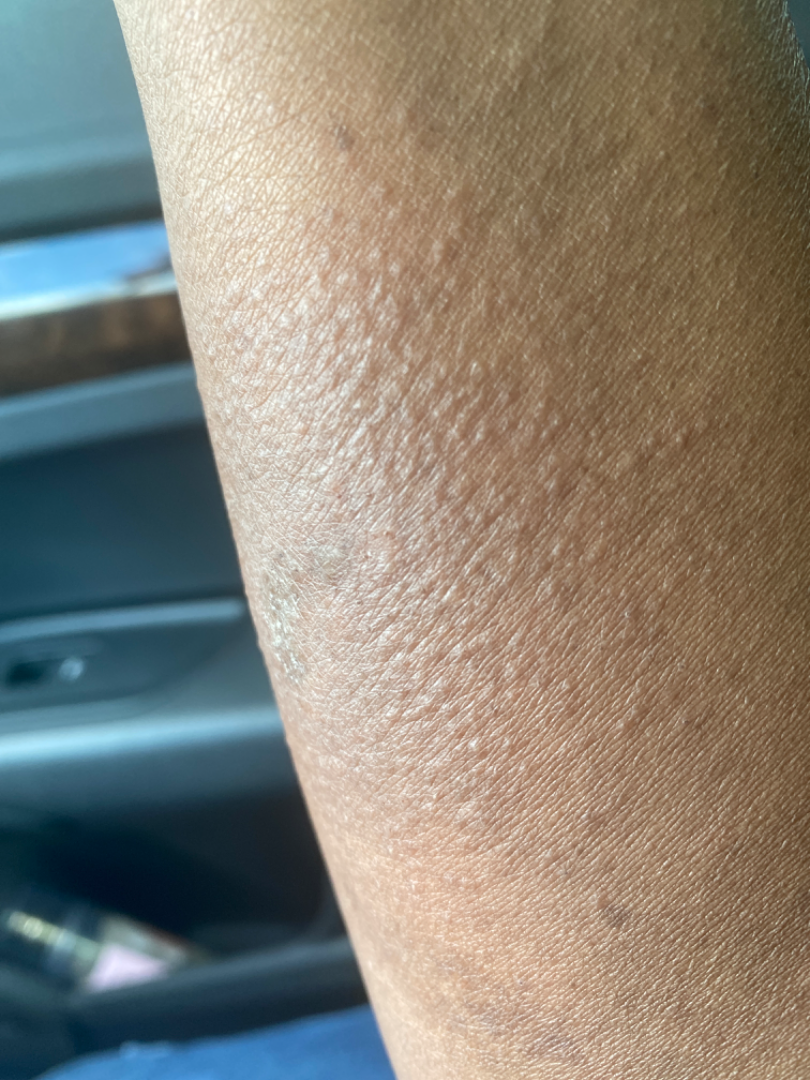Findings:
* assessment: could not be assessed
* associated systemic symptoms: none reported
* described texture: flat
* onset: one to four weeks
* patient describes the issue as: a rash
* framing: at an angle
* affected area: arm